A patient in their 20s; a clinical photograph showing a skin lesion: 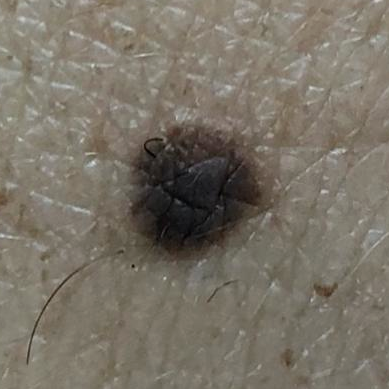  diagnosis:
    name: nevus
    code: NEV
    malignancy: benign
    confirmation: clinical consensus